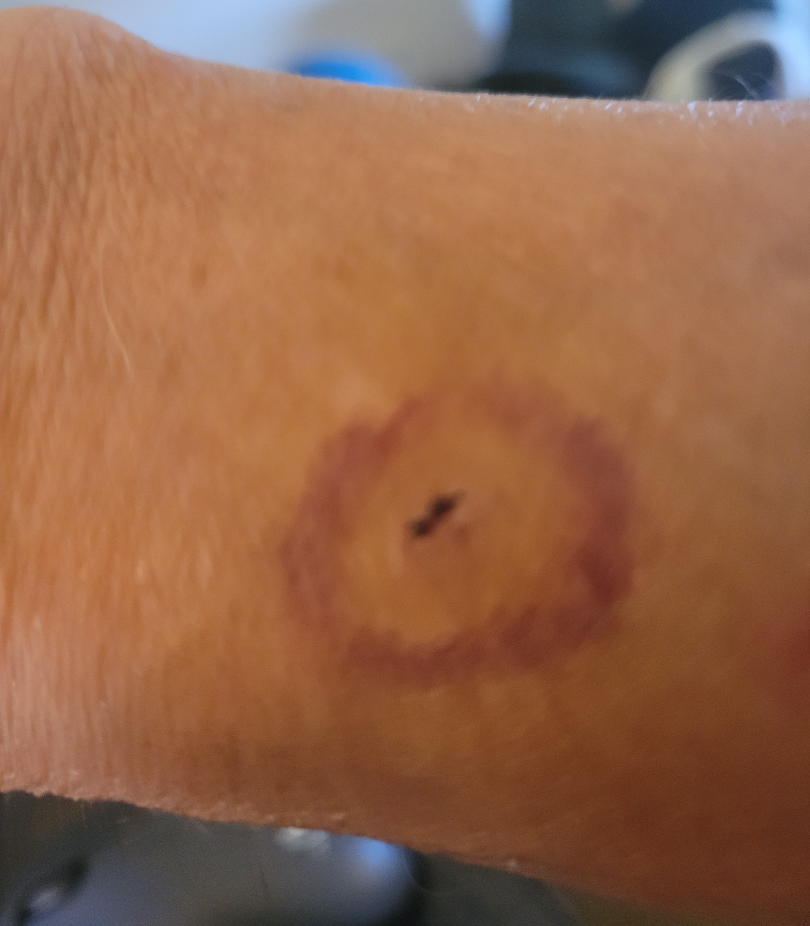Q: Could the case be diagnosed?
A: indeterminate